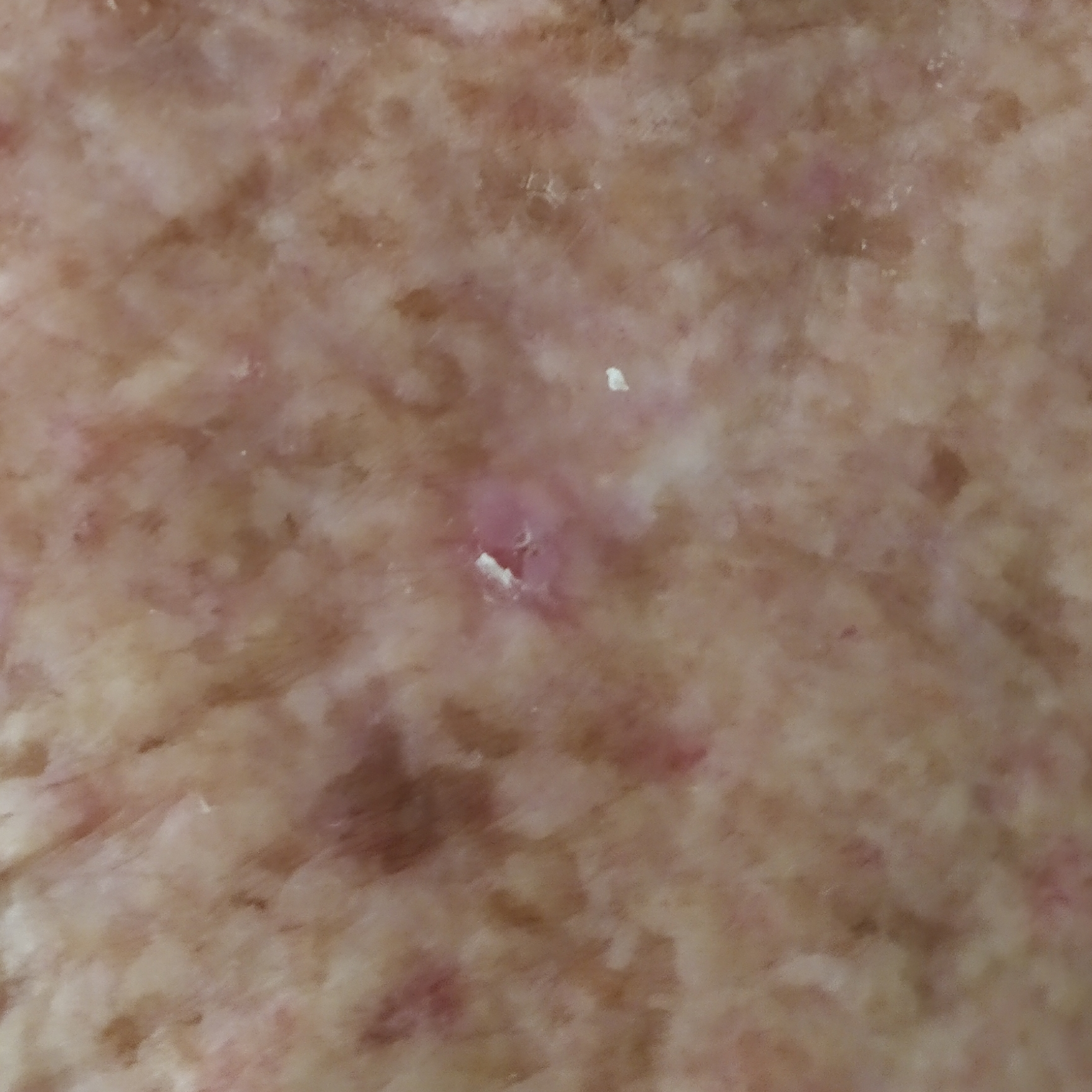modality: smartphone clinical photo; anatomic site: a hand; symptoms: itching / no pain, no change in appearance; diagnostic label: actinic keratosis (clinical consensus).